This is a dermoscopic photograph of a skin lesion — 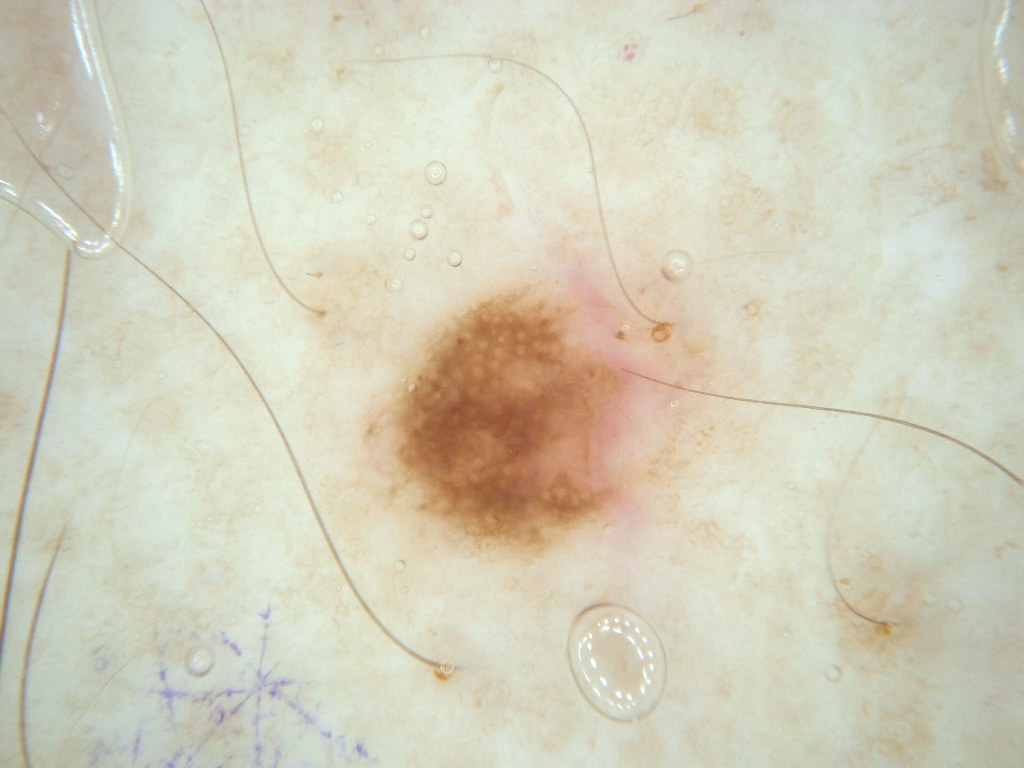As (left, top, right, bottom), the lesion's extent is box(361, 236, 710, 582).
Dermoscopy demonstrates pigment network and globules, with no streaks, negative network, or milia-like cysts.
A mid-sized lesion within the field.
Expert review diagnosed this as a melanocytic nevus, a benign lesion.